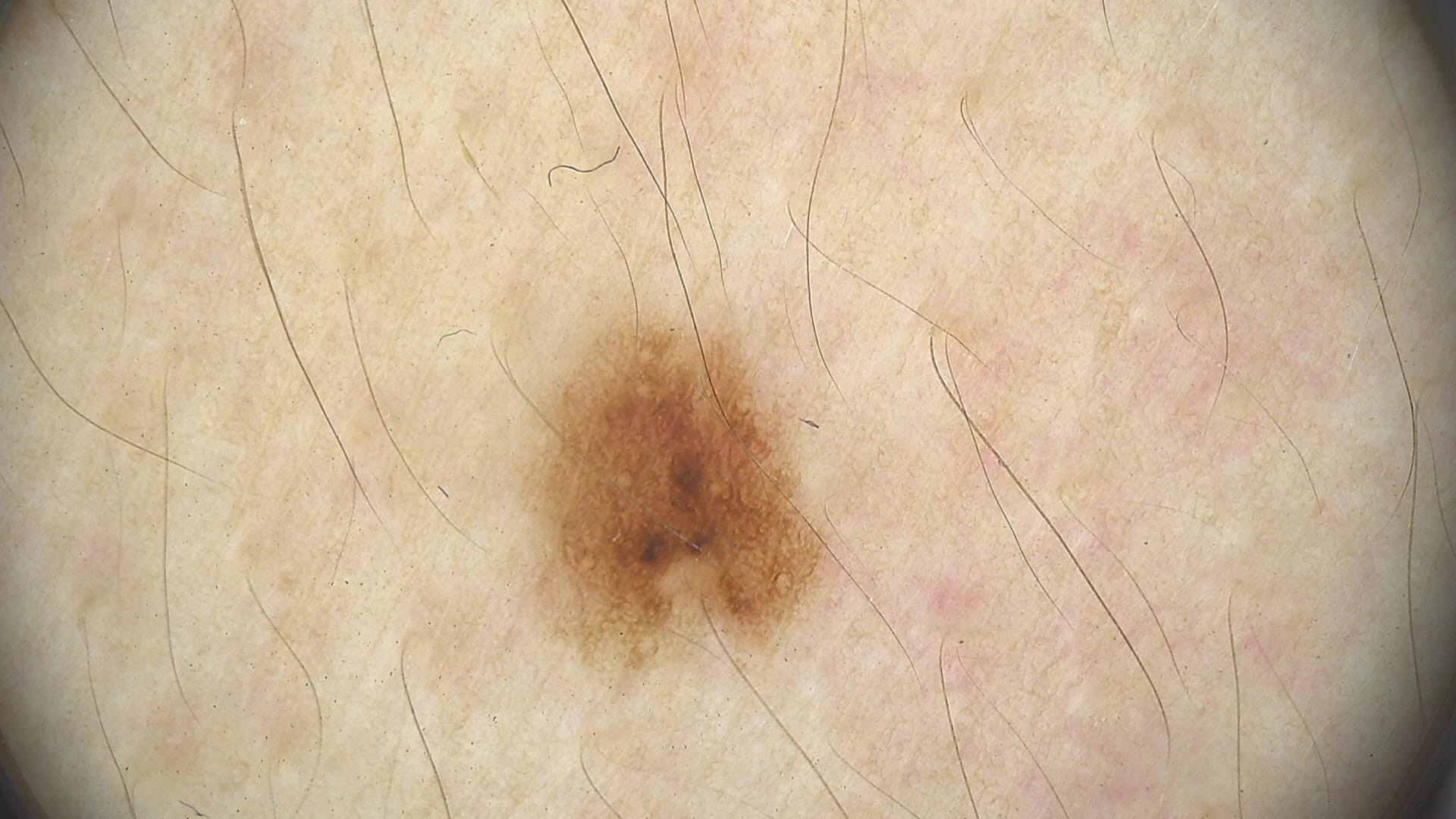A dermoscopic image of a skin lesion. The diagnosis was a benign lesion — a dysplastic junctional nevus.